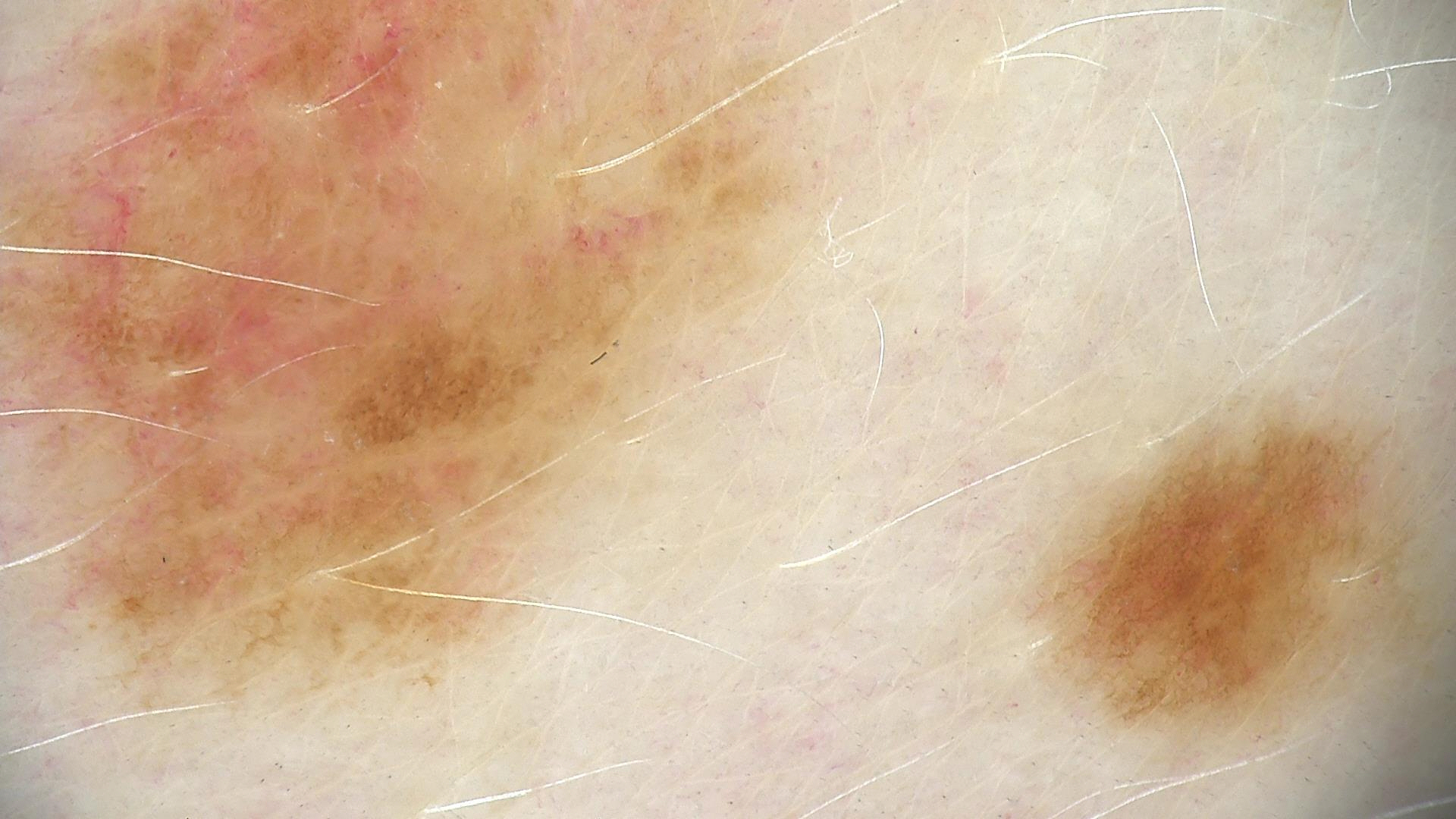A dermoscopic photograph of a skin lesion.
Consistent with a benign lesion — a dysplastic junctional nevus.